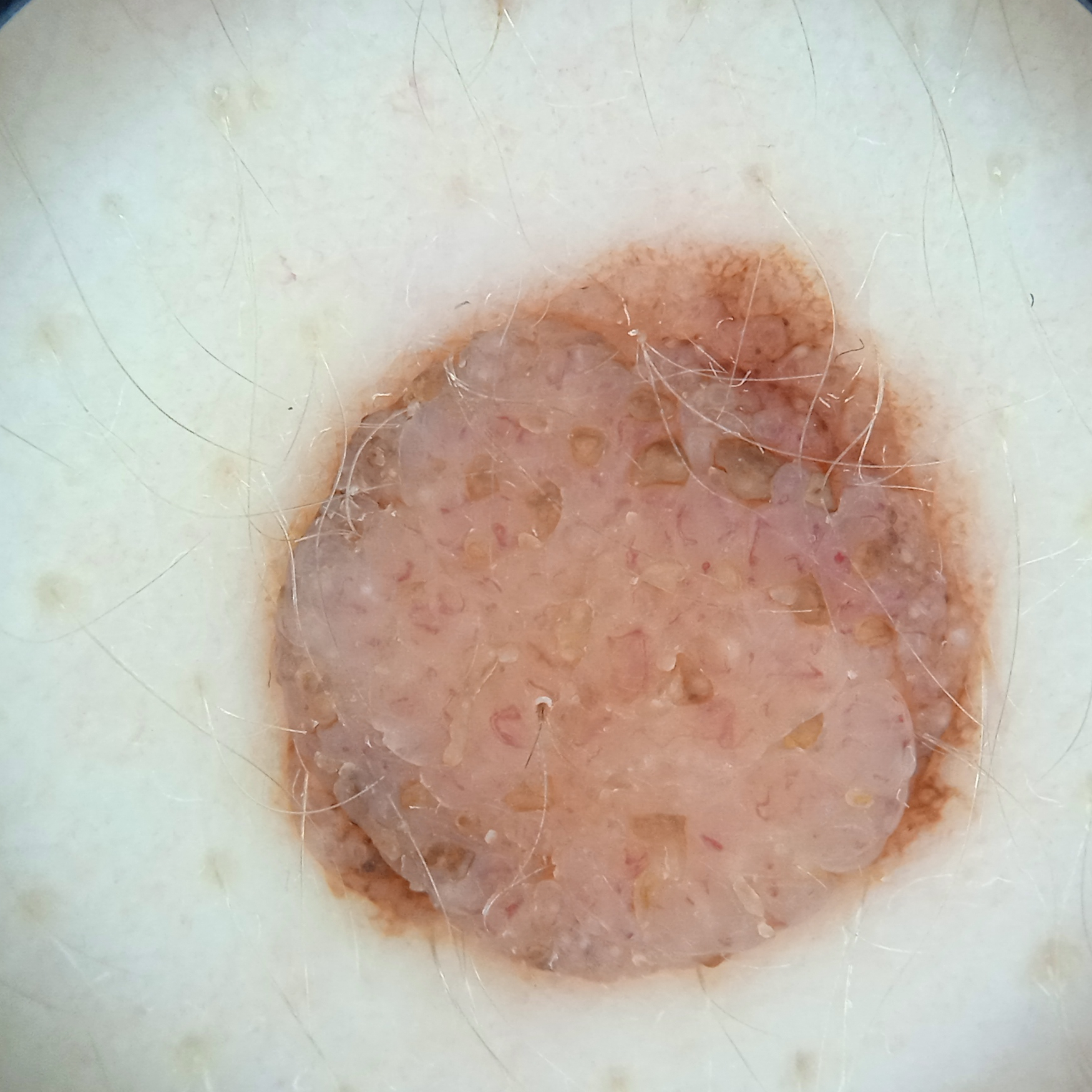– subject · female, 26 years old
– imaging · dermatoscopic image
– location · the back
– diagnosis · melanocytic nevus (dermatologist consensus)